A dermatoscopic image of a skin lesion:
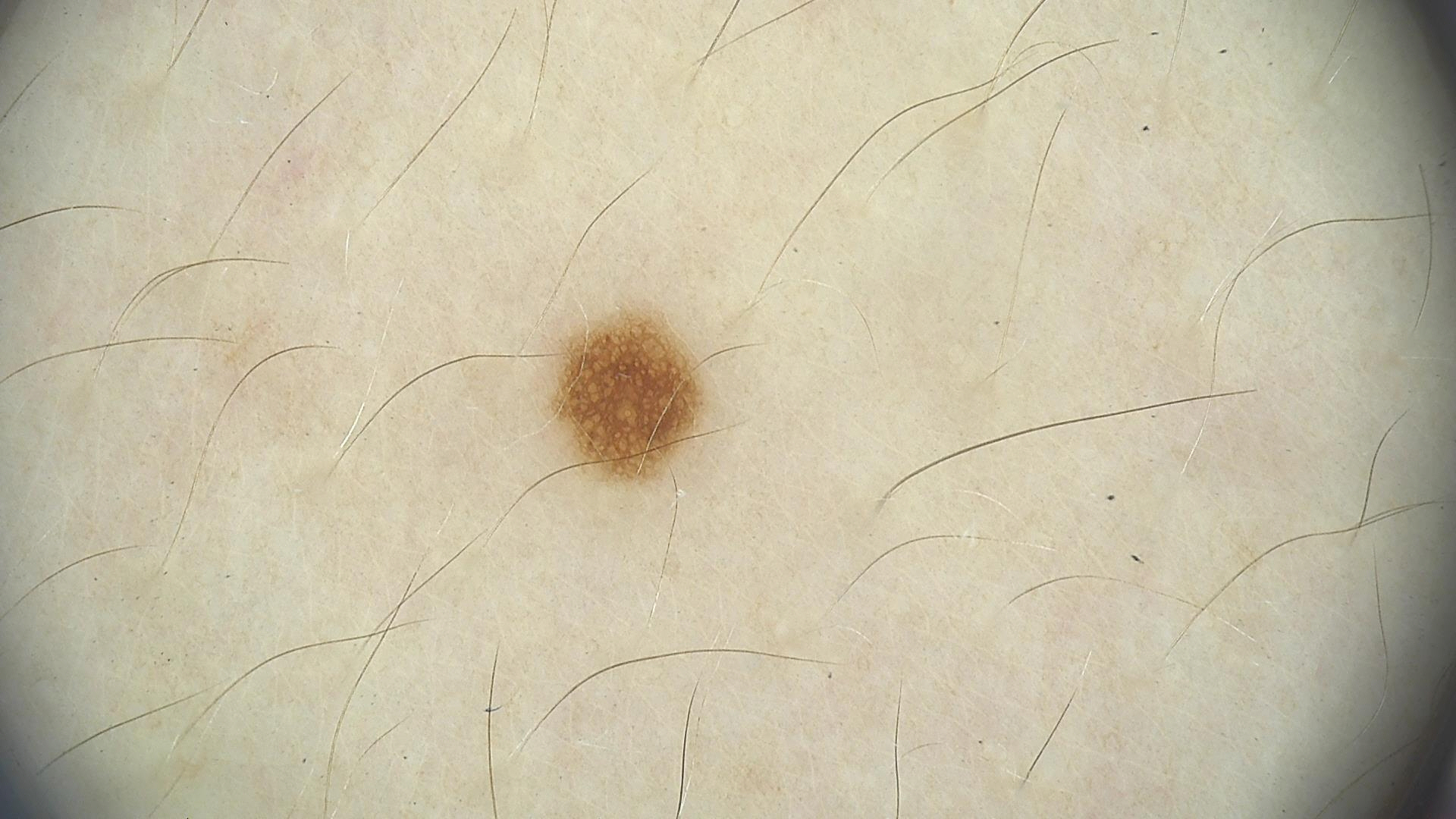Diagnosed as a benign lesion — a dysplastic junctional nevus.